The patient was assessed as skin type II. A contact-polarized dermoscopy image of a skin lesion.
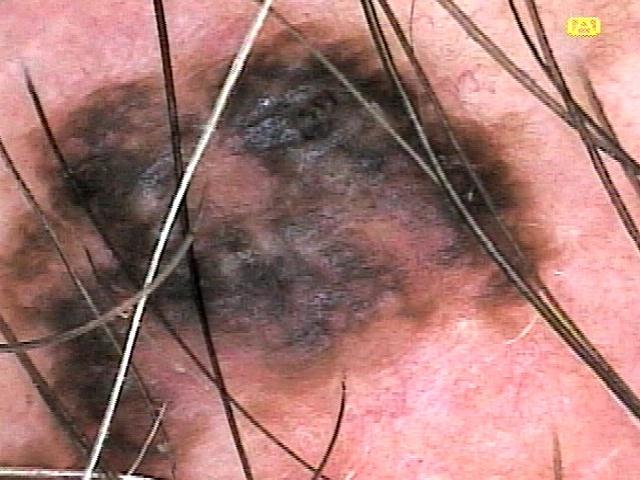Q: What is the anatomic site?
A: the anterior trunk
Q: What is the diagnosis?
A: Seborrheic keratosis (biopsy-proven)